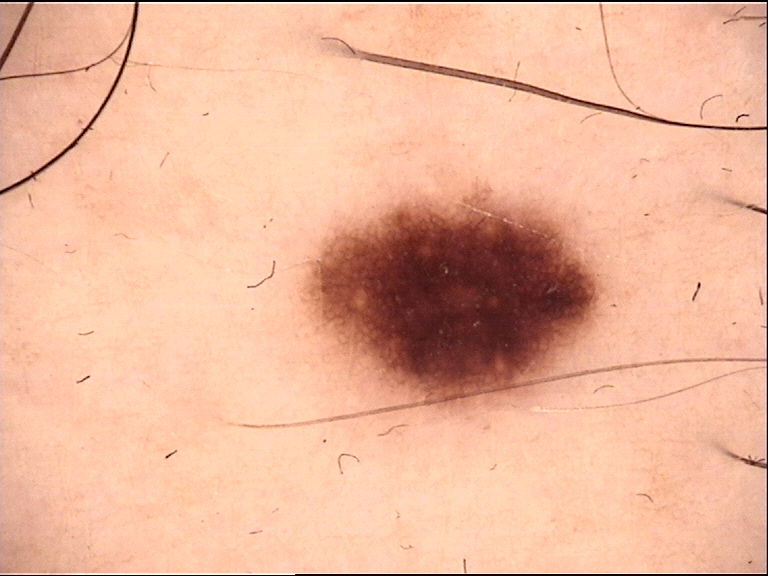Summary:
A dermoscopy image of a single skin lesion.
Conclusion:
The diagnosis was a benign lesion — a dysplastic junctional nevus.